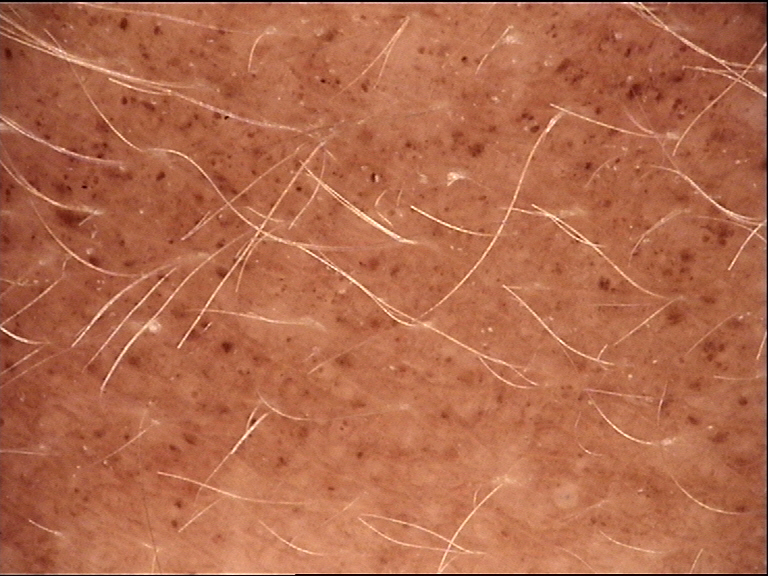Case:
– image type: dermoscopy
– class: congenital junctional nevus (expert consensus)